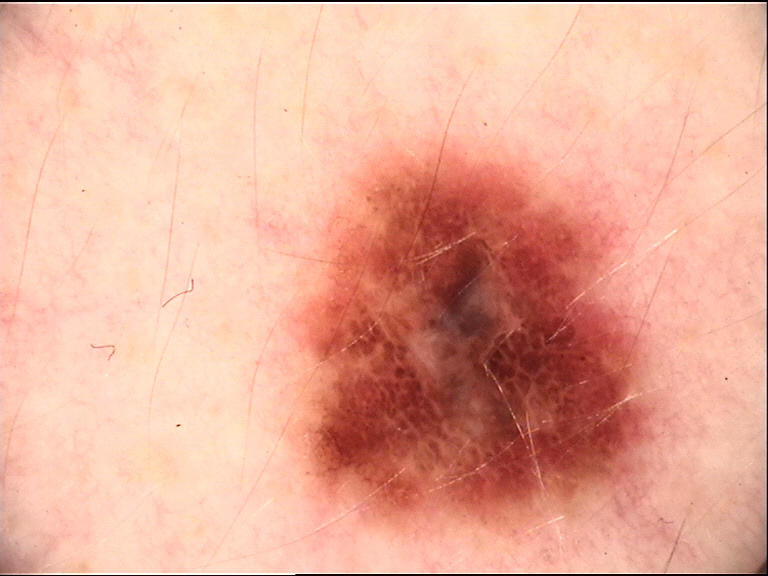Q: What did the workup show?
A: melanoma (biopsy-proven)